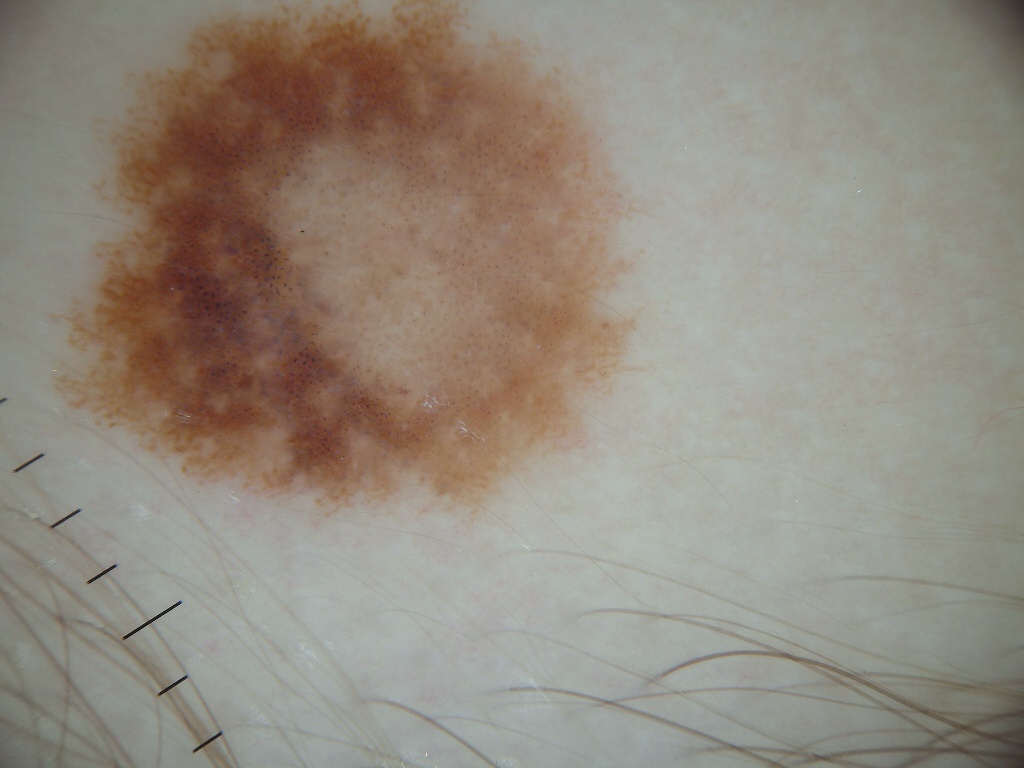image: dermoscopy of a skin lesion | lesion bbox: bbox(40, 3, 668, 537) | diagnosis: a benign lesion.